A dermoscopic photograph of a skin lesion:
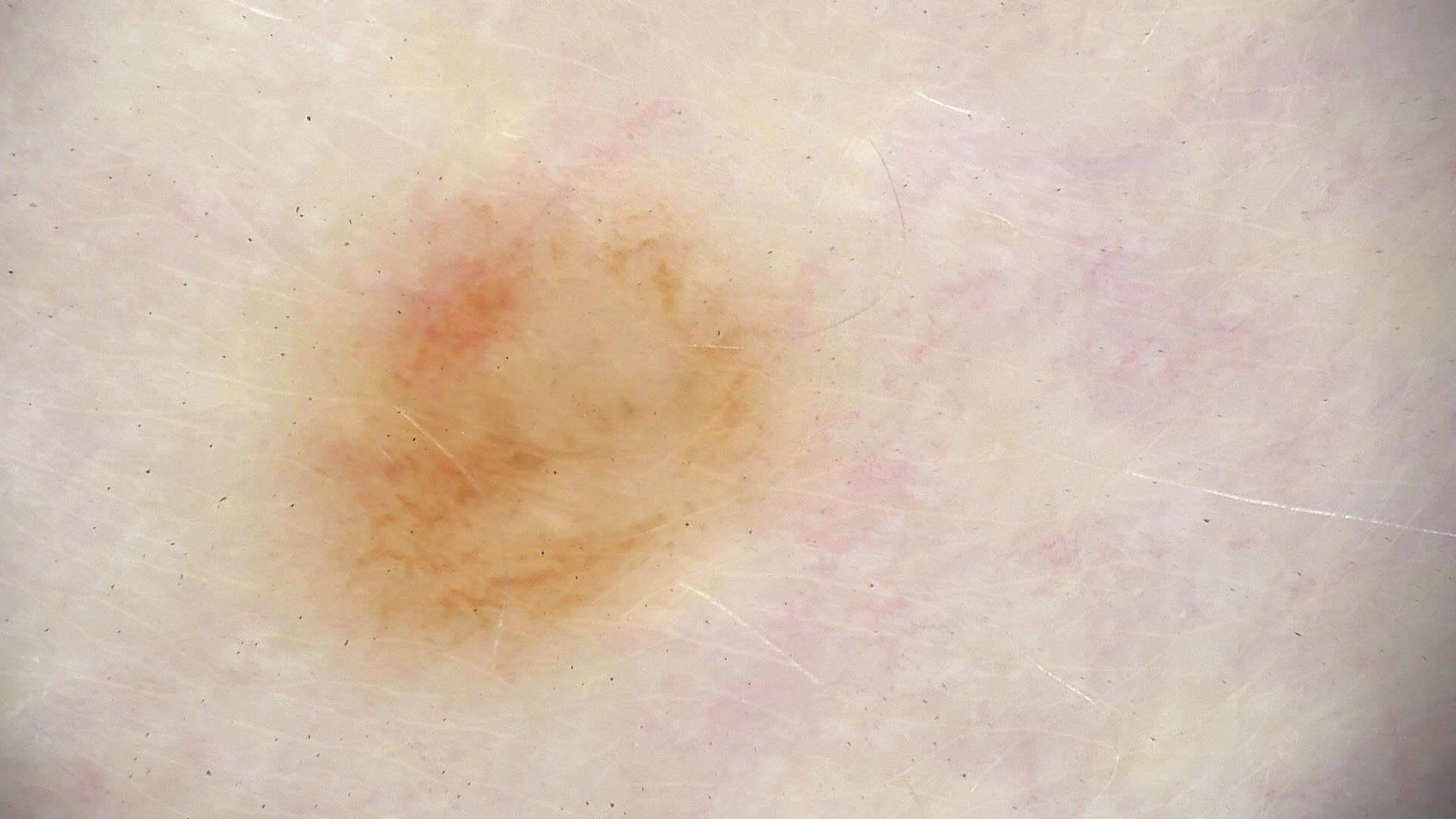label = compound nevus (expert consensus).